A skin lesion imaged with a dermatoscope.
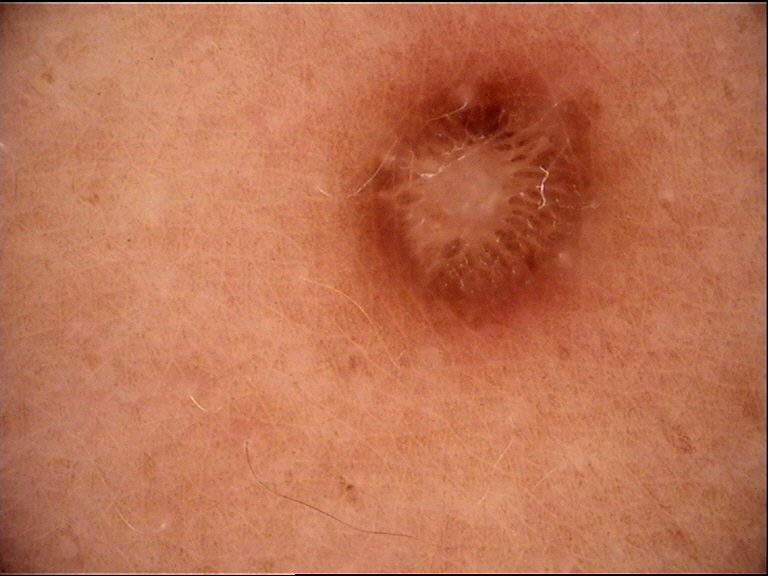This is a fibro-histiocytic lesion. Diagnosed as a benign lesion — a dermatofibroma.